Fitzpatrick skin type V; non-clinician graders estimated a MST of 6. The lesion is described as raised or bumpy. The condition has been present for less than one week. Located on the arm and leg. The photograph is a close-up of the affected area. The subject is 18–29, female — 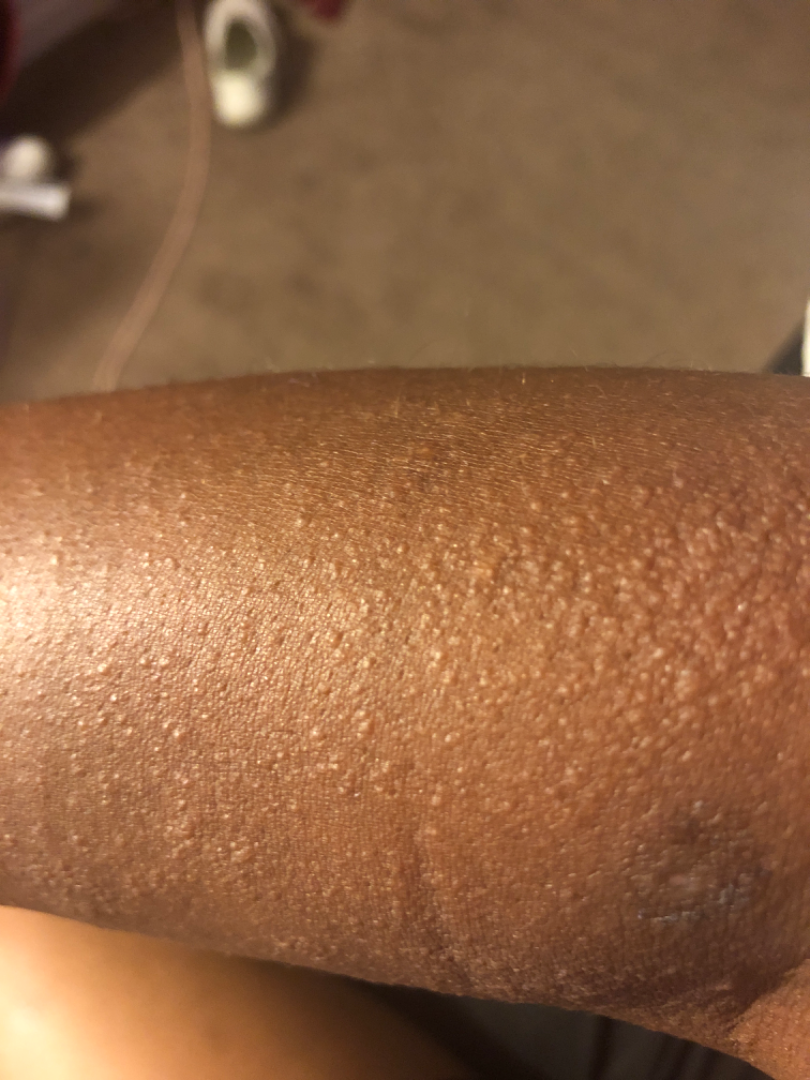Q: What conditions are considered?
A: the differential includes Miliaria and Contact dermatitis, NOS, with no clear leading consideration; less likely is Drug Rash